The lesion involves the front of the torso, arm and head or neck. Reported duration is about one day. The lesion is described as flat. The contributor is female. The photo was captured at an angle. Symptoms reported: itching, bothersome appearance and burning.
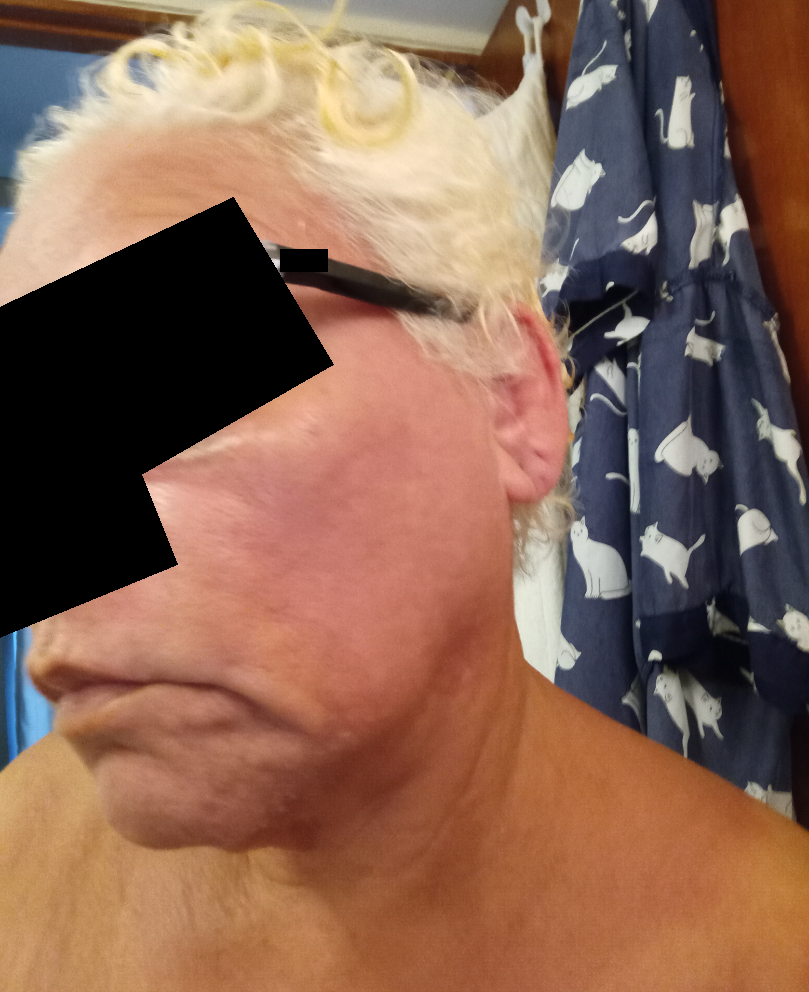impression: Photodermatitis (possible); Vitiligo (possible)